This image was taken at a distance; located on the leg: 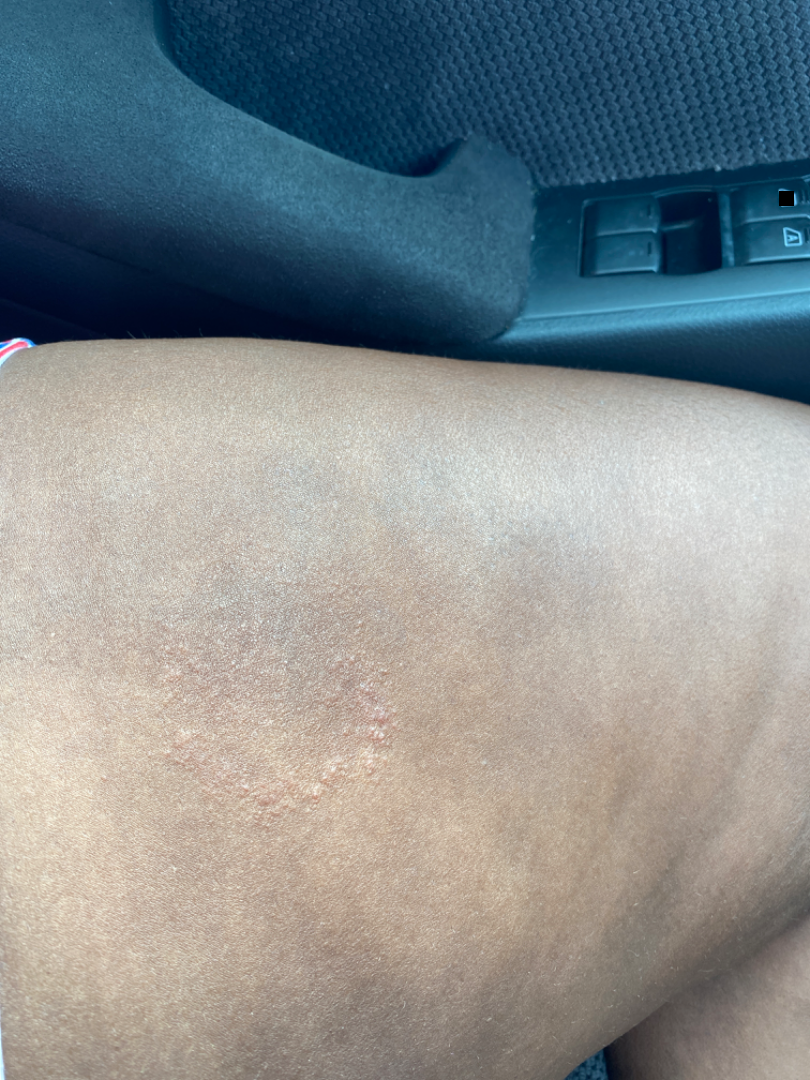| feature | finding |
|---|---|
| impression | the favored diagnosis is Tinea; with consideration of Lichen planus/lichenoid eruption; an alternative is Eczema |